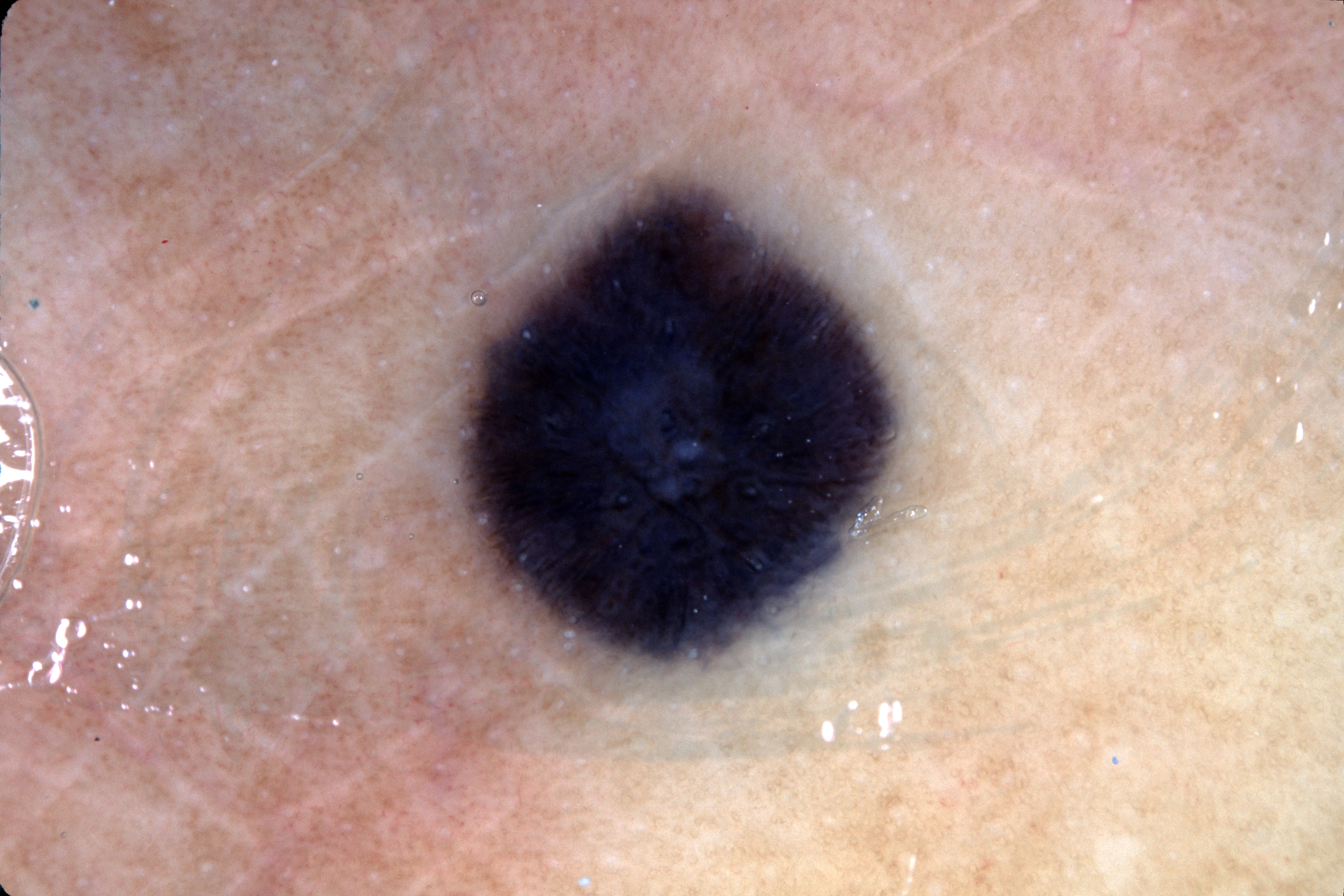A dermoscopic image of a skin lesion. A moderately sized lesion. The lesion's extent is x1=473, y1=203, x2=882, y2=651. Dermoscopic examination shows streaks. The lesion was assessed as a melanocytic nevus, a benign lesion.